Imaged for a research study, with no referral diagnosis recorded · on a questionnaire the patient reported no sunbed use and no personal history of cancer · the patient says their skin reddens painfully with sun exposure · a female subject age 50 · a clinical photograph of a skin lesion · the patient describes having a moderate number of moles — 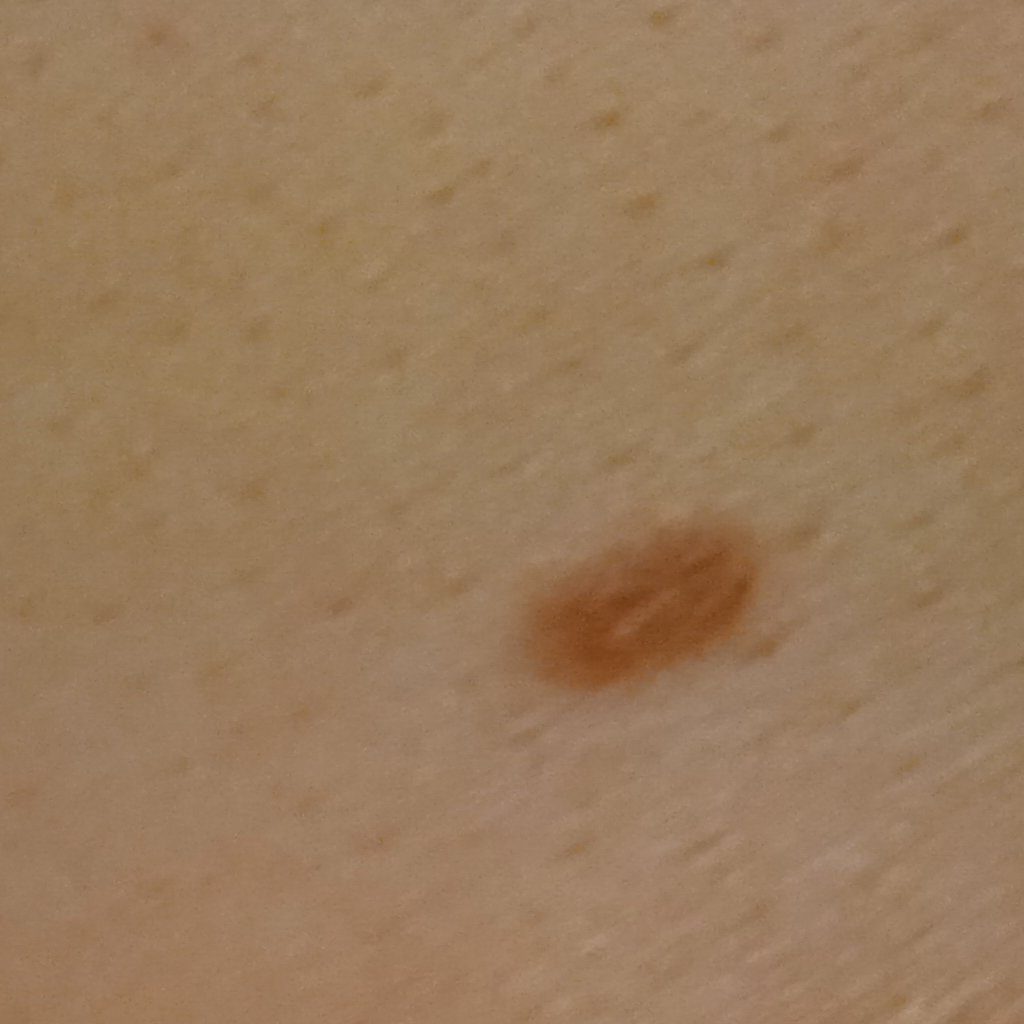site: the torso; size: 4.9 mm; diagnosis: melanocytic nevus (dermatologist consensus).